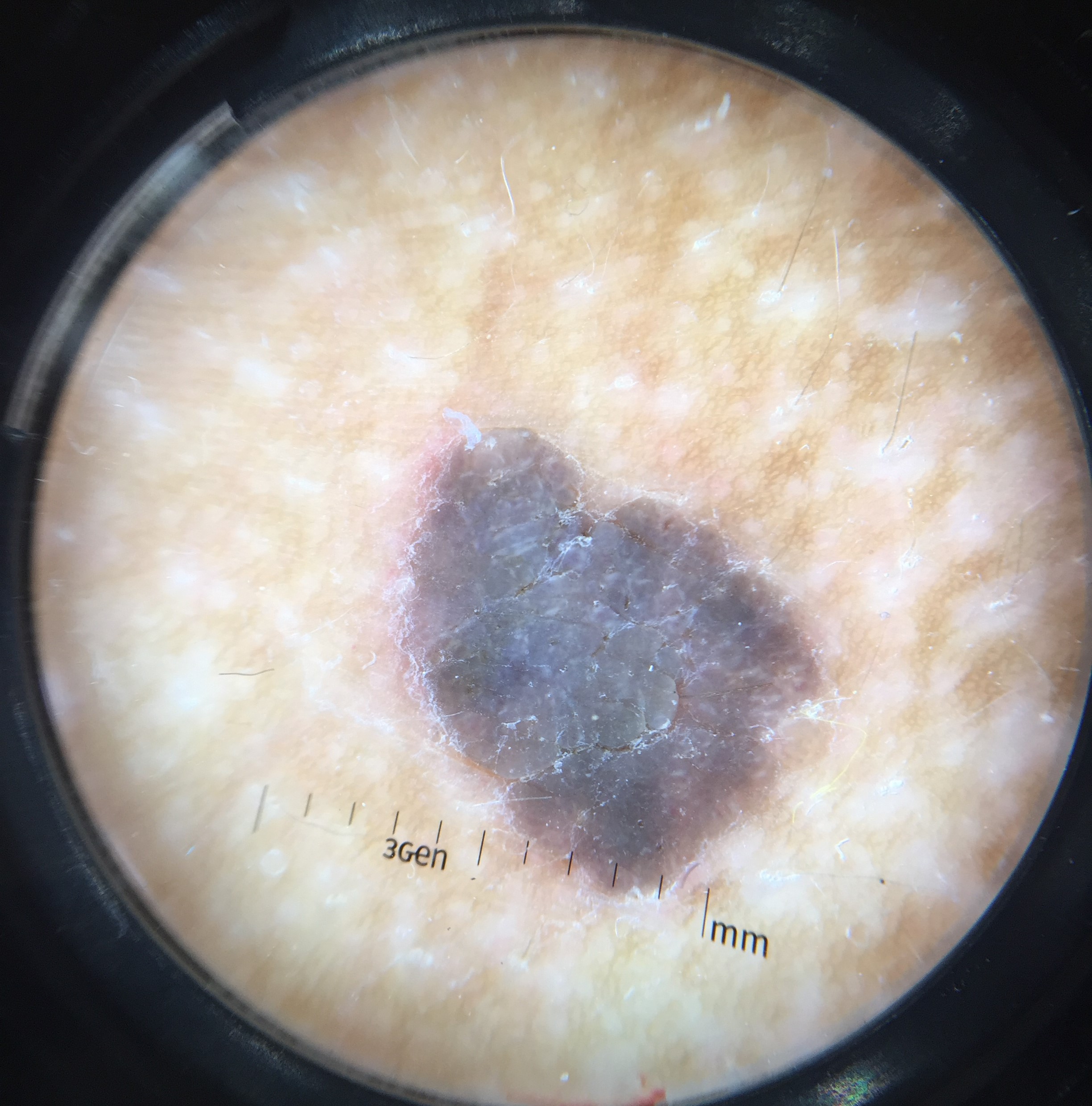image = dermatoscopy
assessment = seborrheic keratosis (expert consensus)